This is a close-up image. Male contributor, age 18–29. The lesion involves the back of the hand:
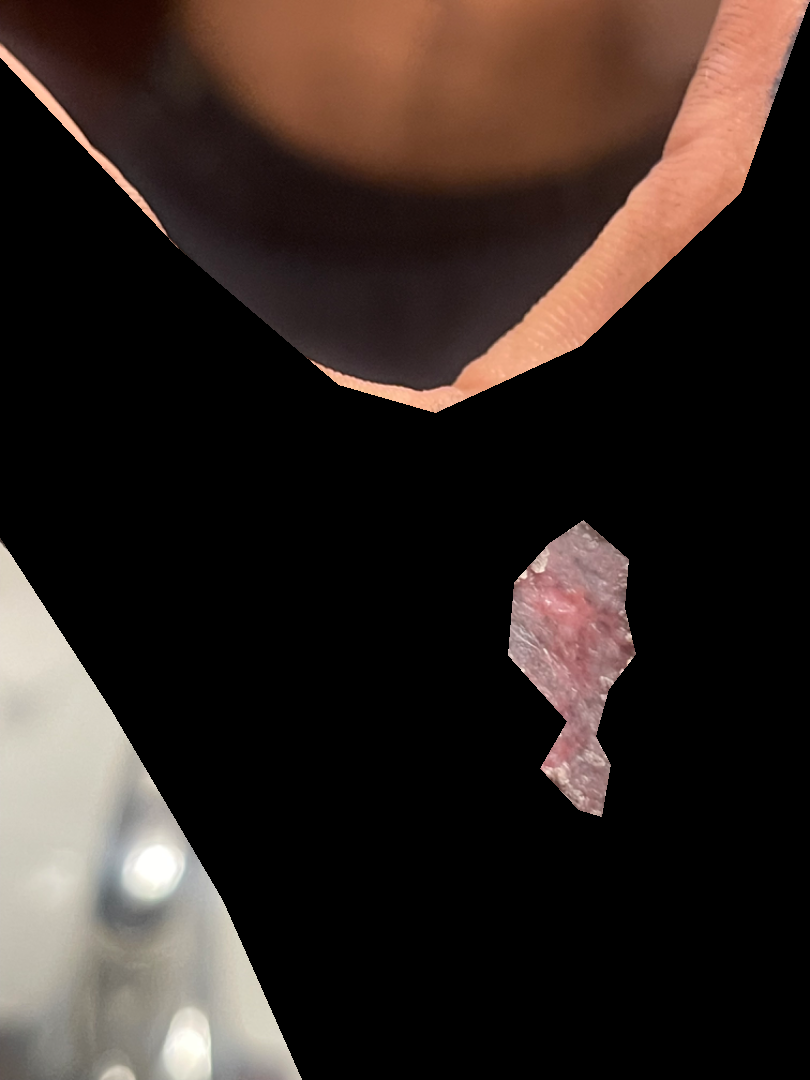The skin findings could not be characterized from the image.
Reported lesion symptoms include itching and pain.
The condition has been present for less than one week.
The patient described the issue as skin that appeared healthy to them.
Texture is reported as rough or flaky.